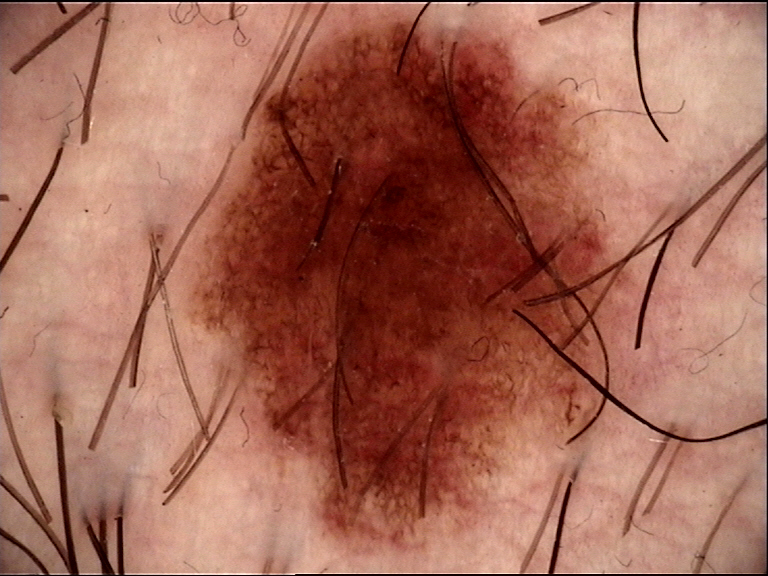A dermoscopic close-up of a skin lesion.
The diagnosis was a benign lesion — a dysplastic junctional nevus.